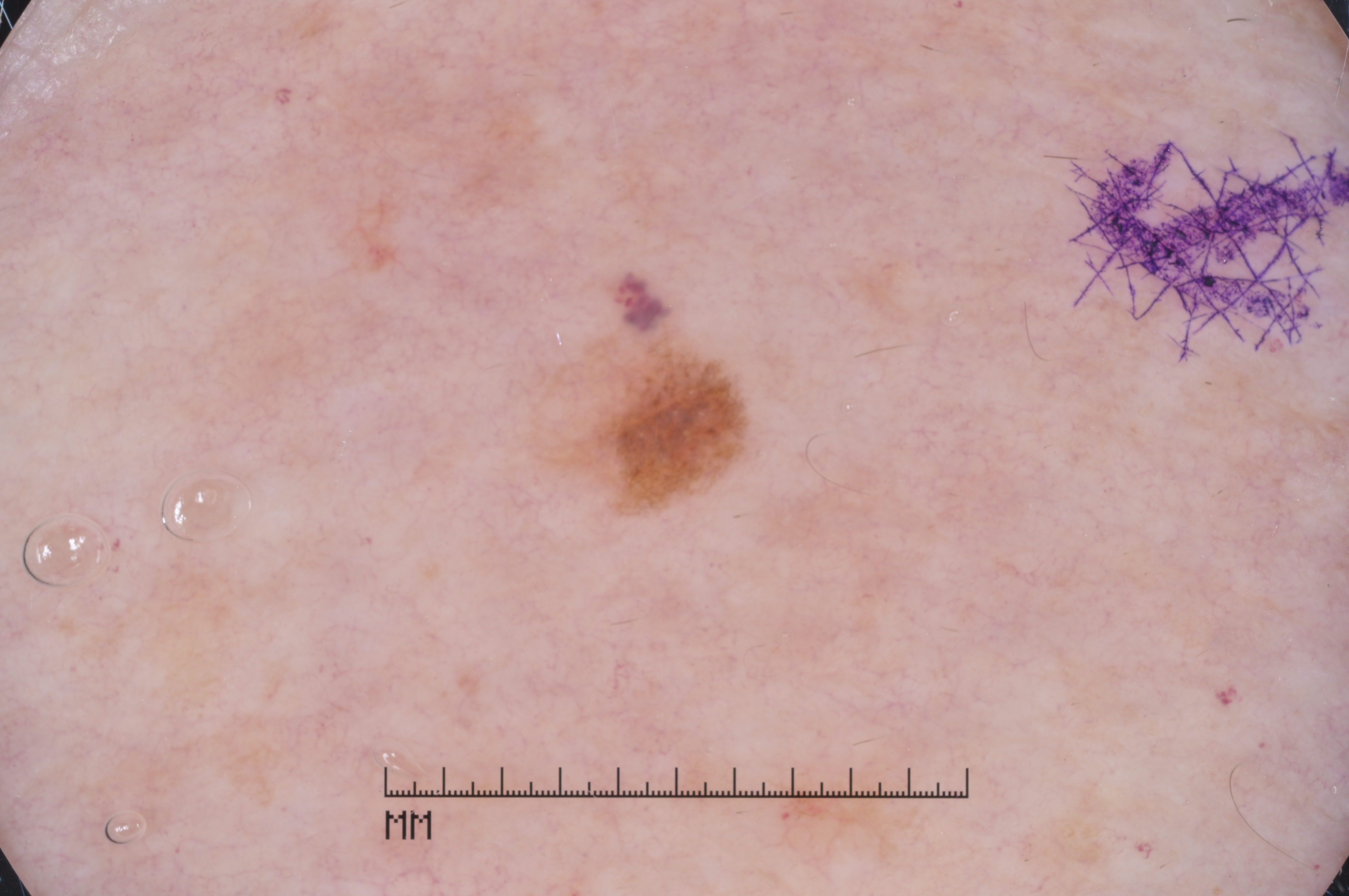A female subject, aged 63 to 67.
A dermatoscopic image of a skin lesion.
Dermoscopy demonstrates milia-like cysts.
The lesion occupies the region x1=559 y1=322 x2=748 y2=504.
The lesion covers approximately 2% of the dermoscopic field.
Biopsy-confirmed as a melanoma.